Present for about one day, FST III, the photo was captured at a distance, the affected area is the leg and arm.
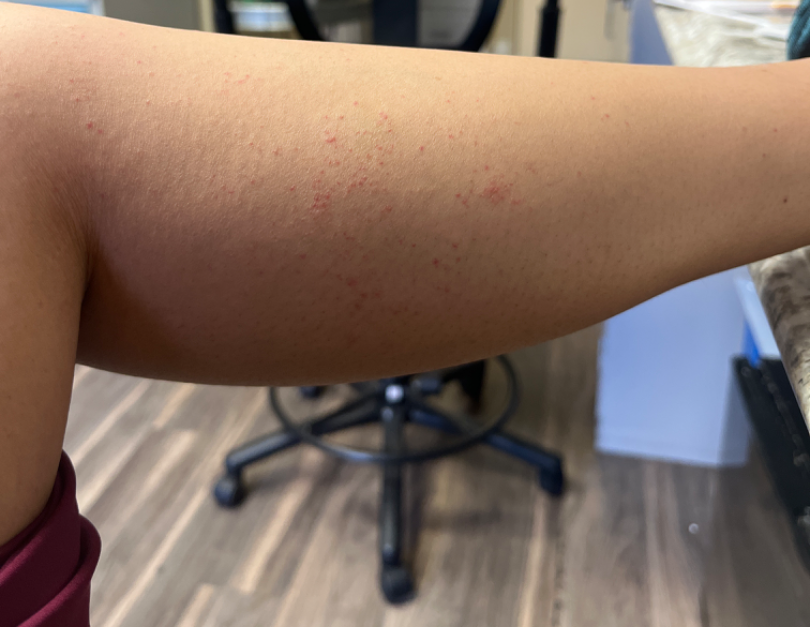Findings:
– clinical impression — single-reviewer assessment: the differential, in no particular order, includes Pigmented purpuric eruption, Eczema and Allergic Contact Dermatitis